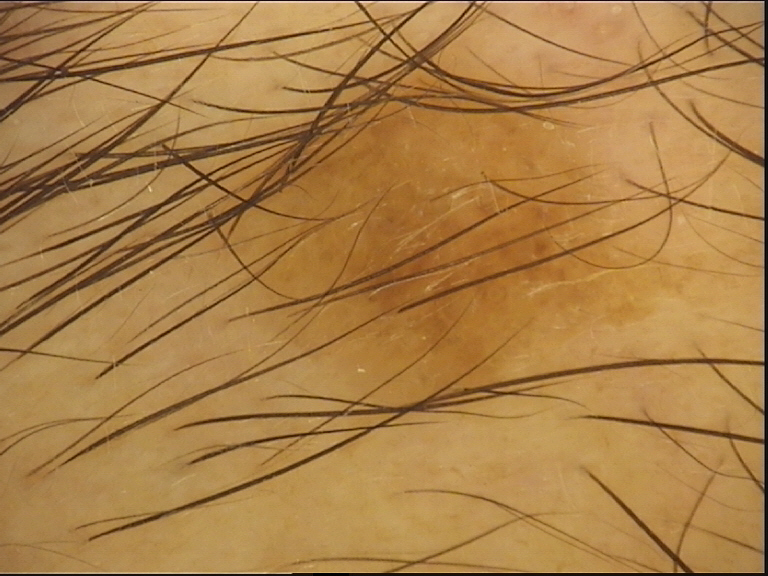Impression:
Classified as a seborrheic keratosis.